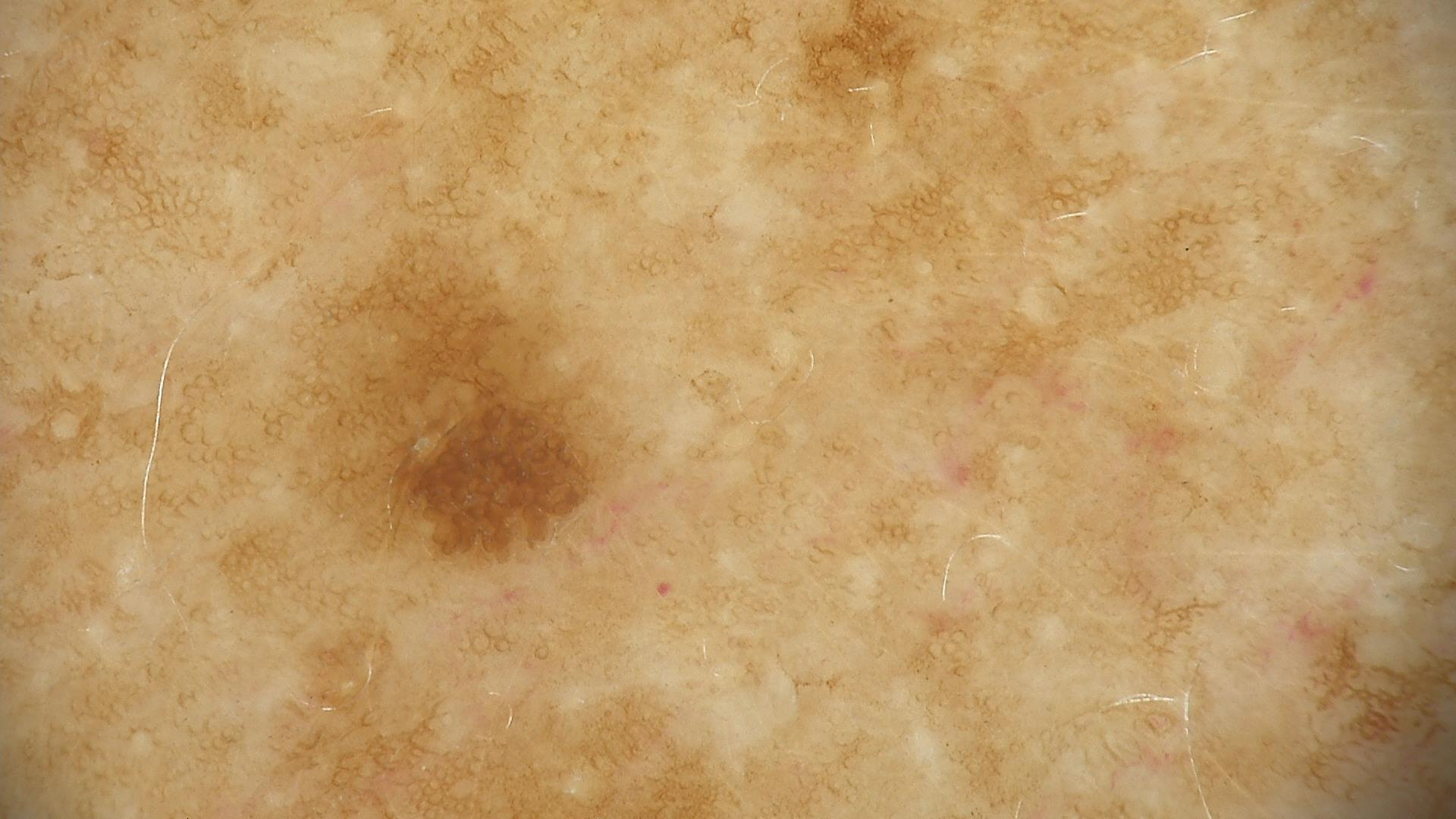Q: What is the diagnosis?
A: seborrheic keratosis (expert consensus)